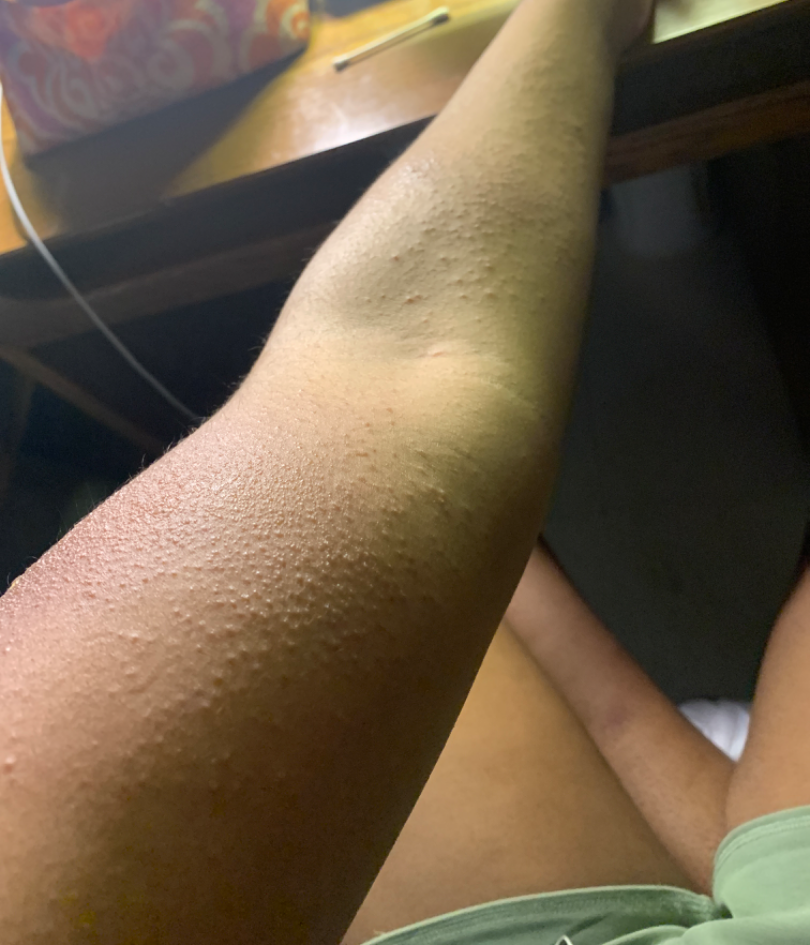Case summary:
• present for: less than one week
• shot type: at an angle
• body site: arm
• lesion texture: rough or flaky, raised or bumpy and fluid-filled
• subject: female, age 18–29
• assessment: the reviewer's impression was Allergic Contact Dermatitis